A skin lesion imaged with a dermatoscope.
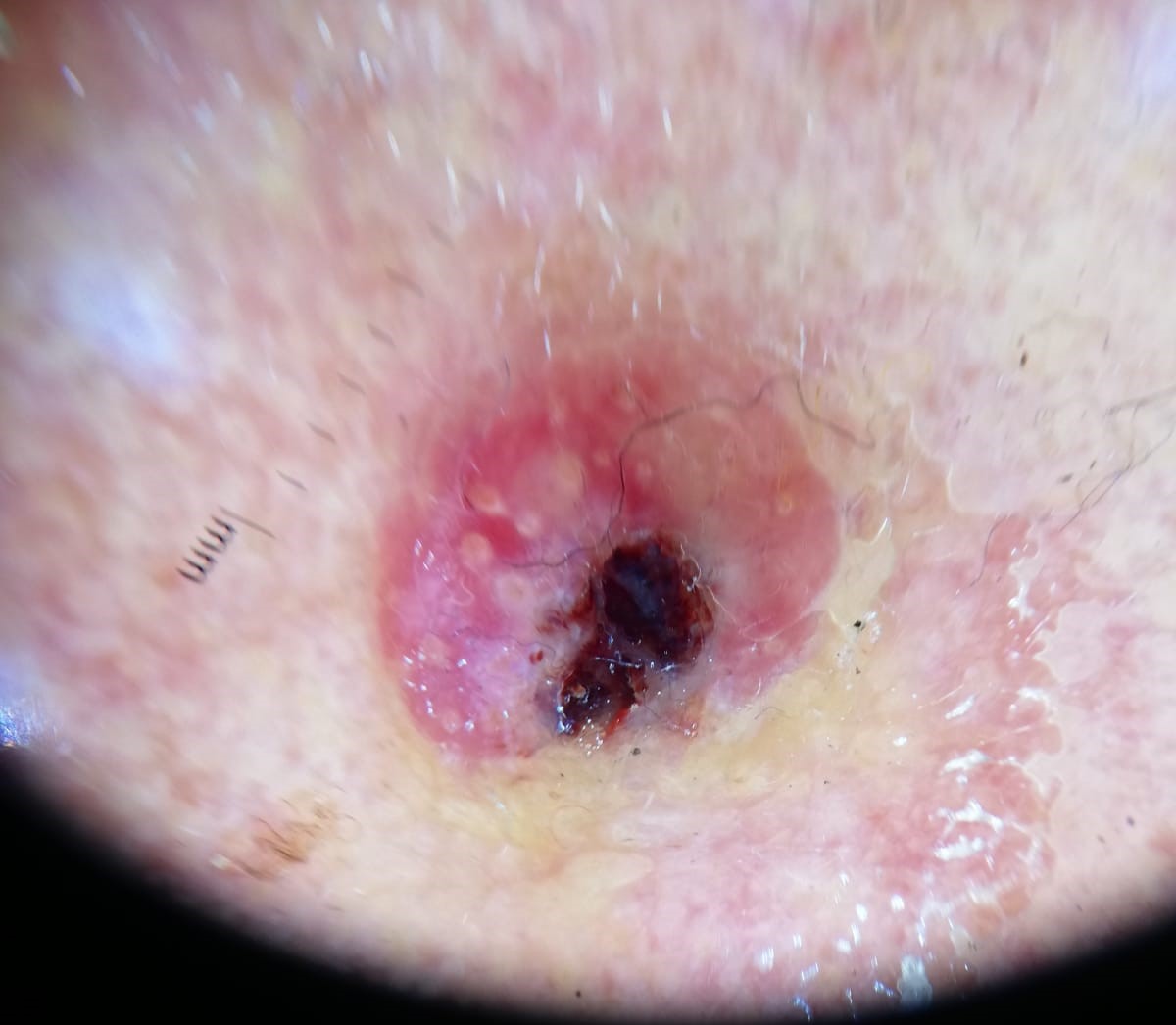diagnostic label: squamous cell carcinoma (biopsy-proven).